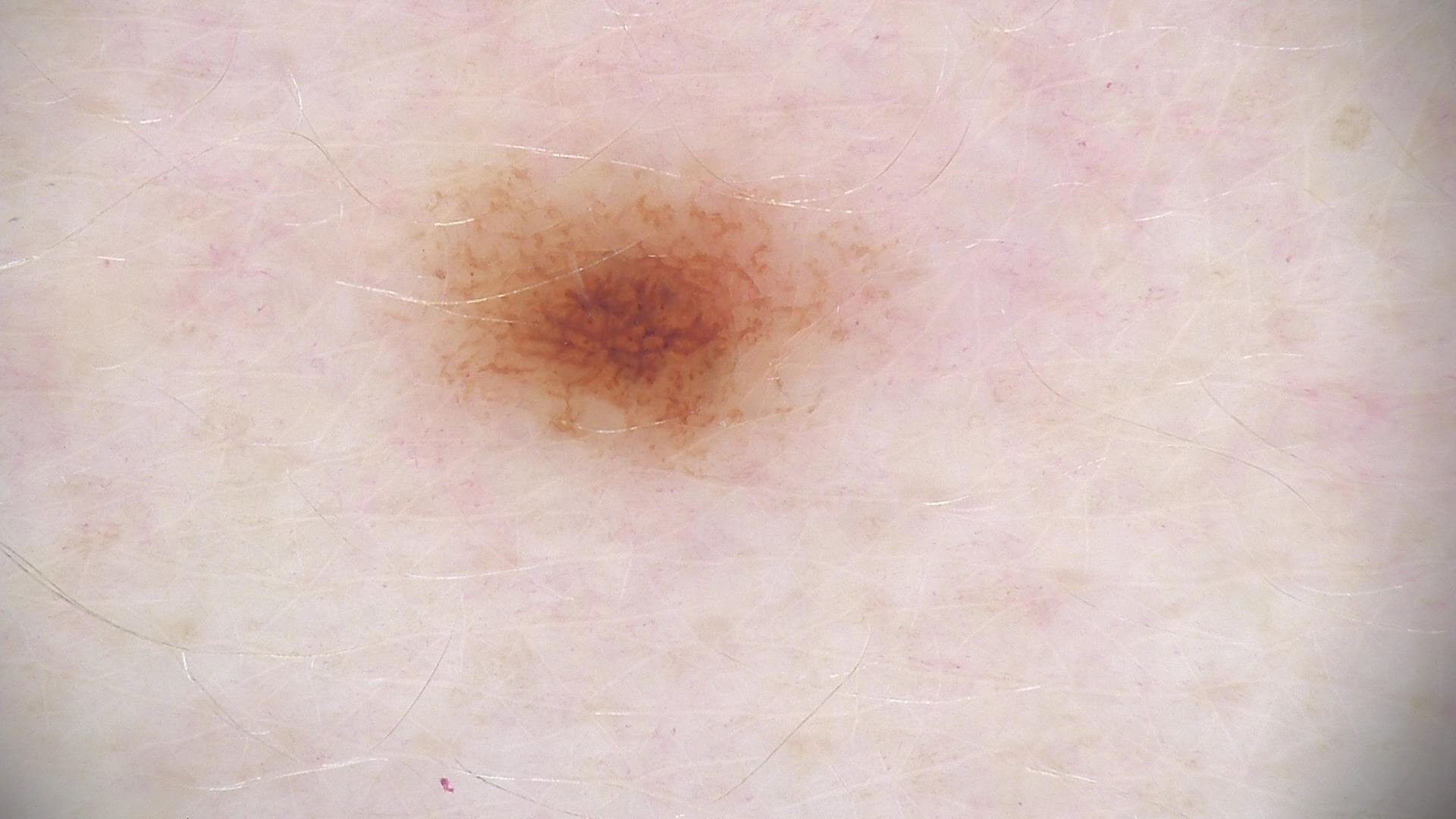Classified as a dysplastic junctional nevus.